Dermoscopy of a skin lesion. A male patient, aged approximately 50:
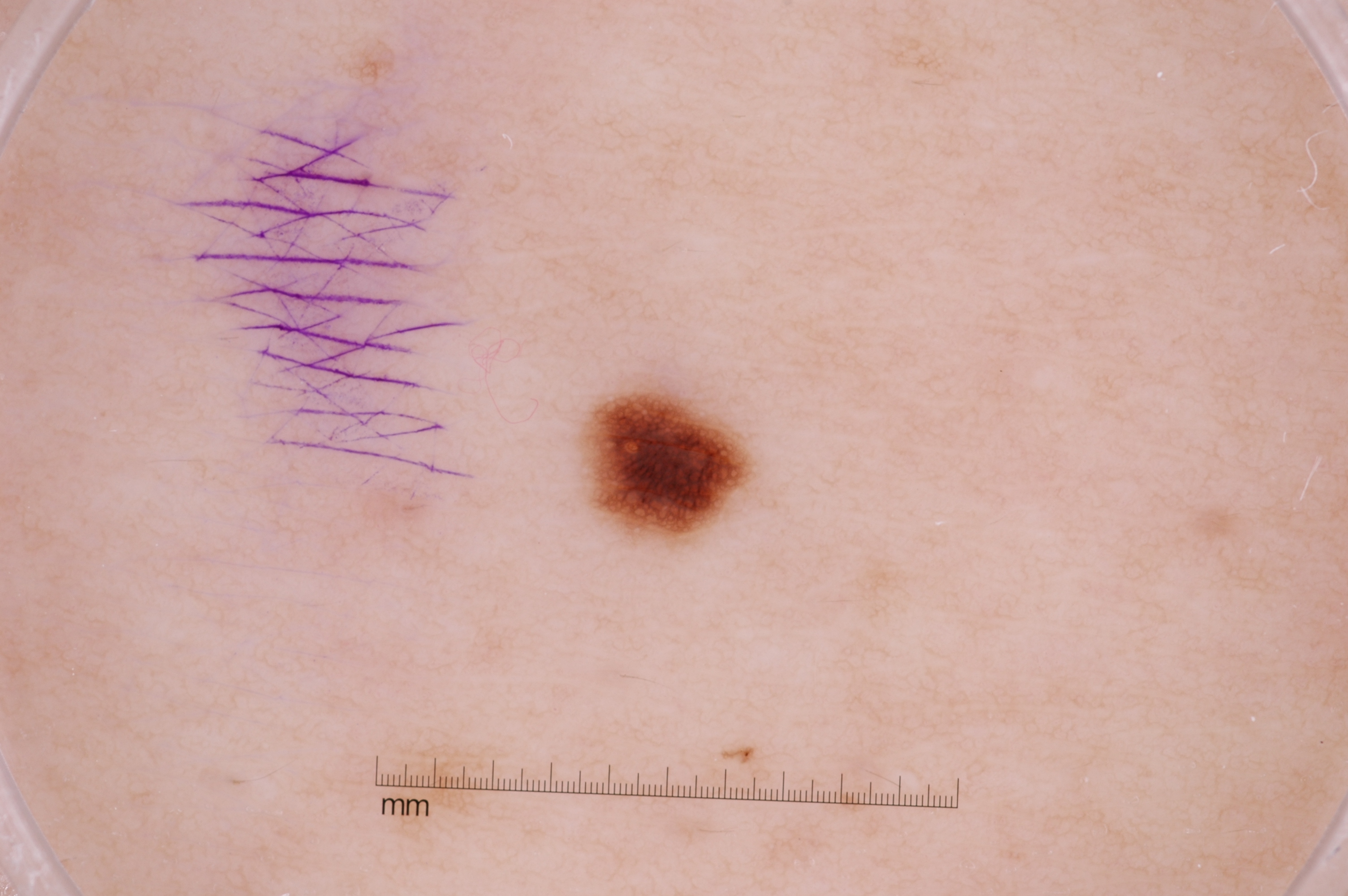The lesion occupies roughly 1% of the field. Dermoscopically, the lesion shows pigment network, with no negative network, streaks, or milia-like cysts. The lesion spans <bbox>590, 392, 747, 539</bbox>. The clinical diagnosis was a melanocytic nevus, a benign skin lesion.